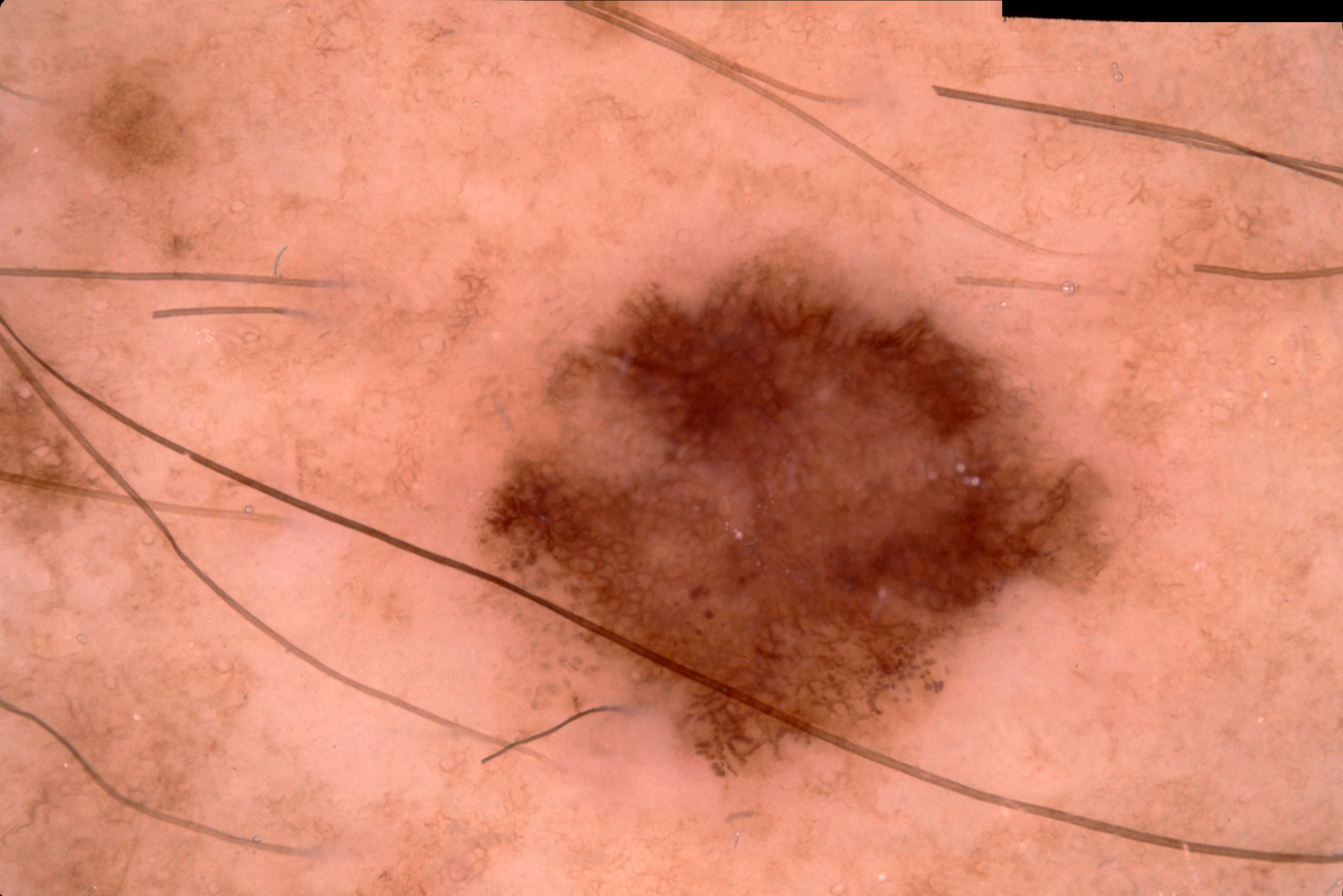Dermoscopy of a skin lesion.
A male patient.
Lesion location: x1=493 y1=259 x2=1112 y2=770.
A moderately sized lesion.
Dermoscopic assessment notes pigment network; no streaks, negative network, or milia-like cysts.
The lesion was assessed as a melanocytic nevus, a benign lesion.